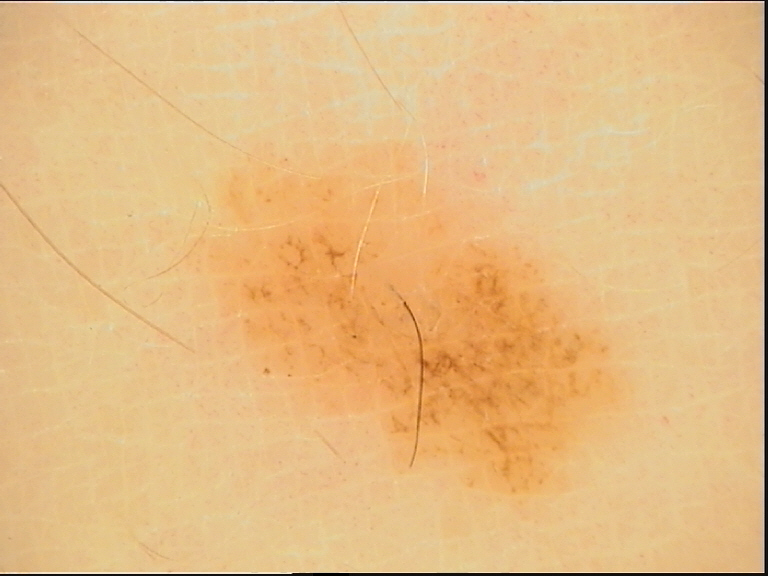diagnosis = dysplastic junctional nevus (expert consensus).